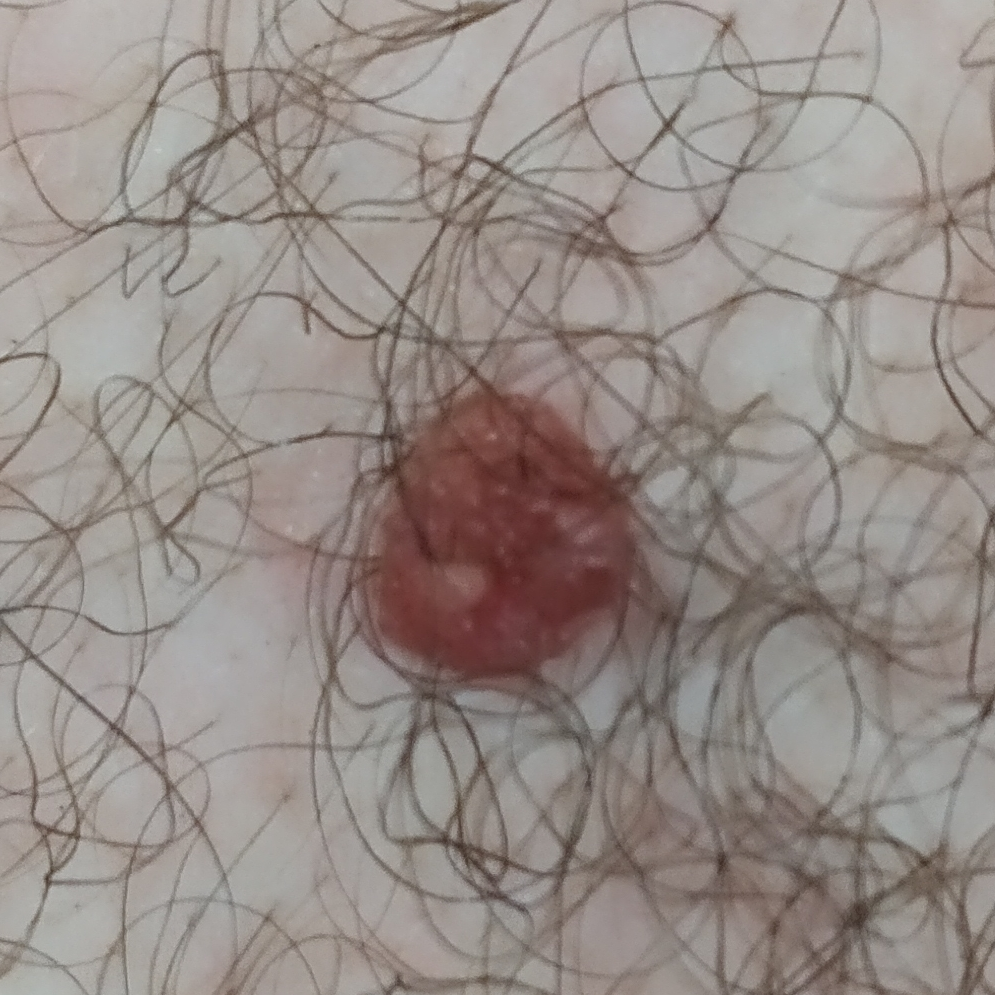A subject aged 26. A clinical photograph of a skin lesion. The lesion involves the chest. Consistent with a nevus.